A female subject aged 26: 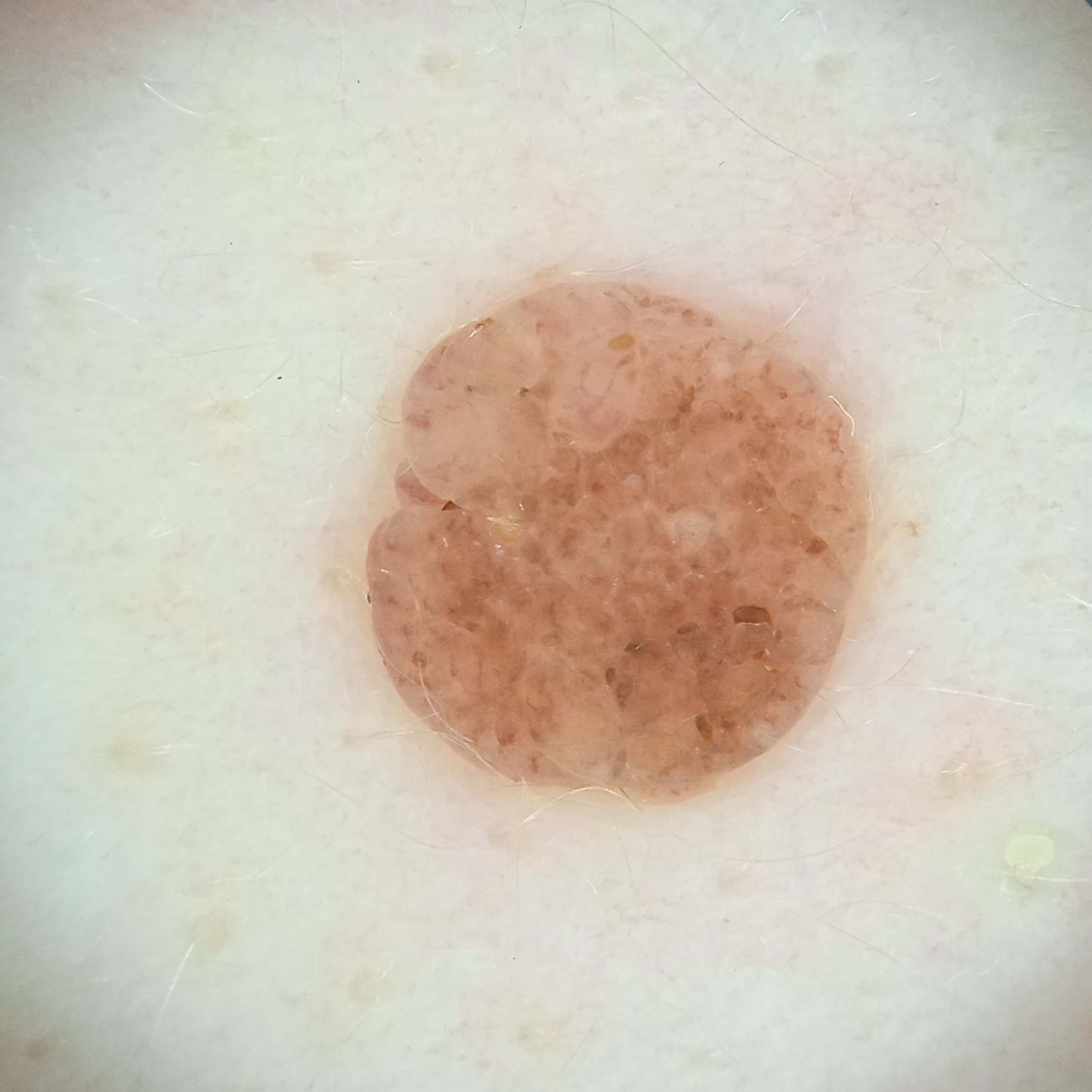Findings:
* anatomic site — the back
* lesion size — 5.6 mm
* diagnostic label — melanocytic nevus (dermatologist consensus)